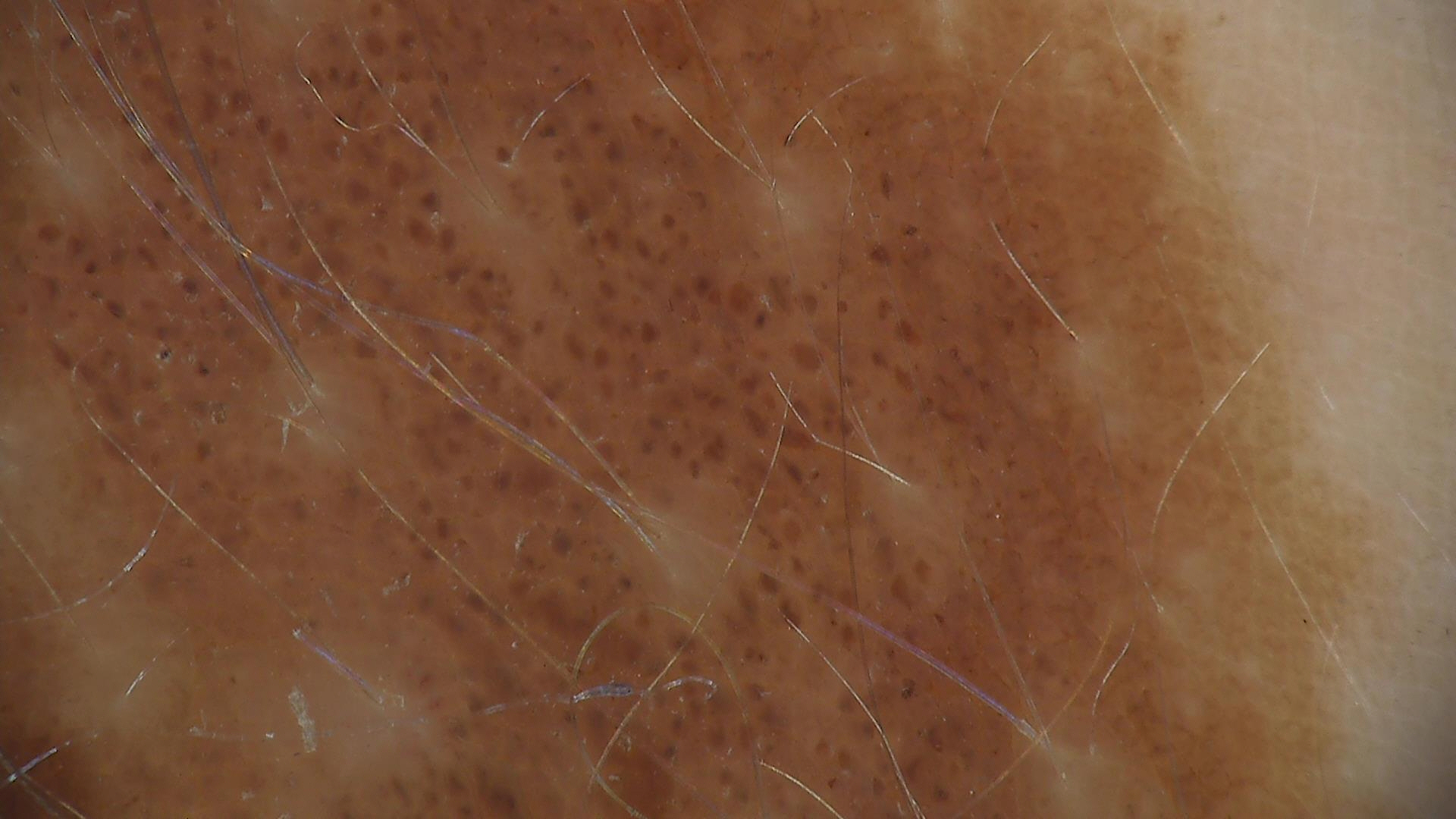A dermoscopic close-up of a skin lesion. This is a banal lesion. The diagnostic label was a congenital junctional nevus.